The contributor is 60–69, female · the back of the torso, front of the torso, head or neck and arm are involved · the photo was captured at an angle — 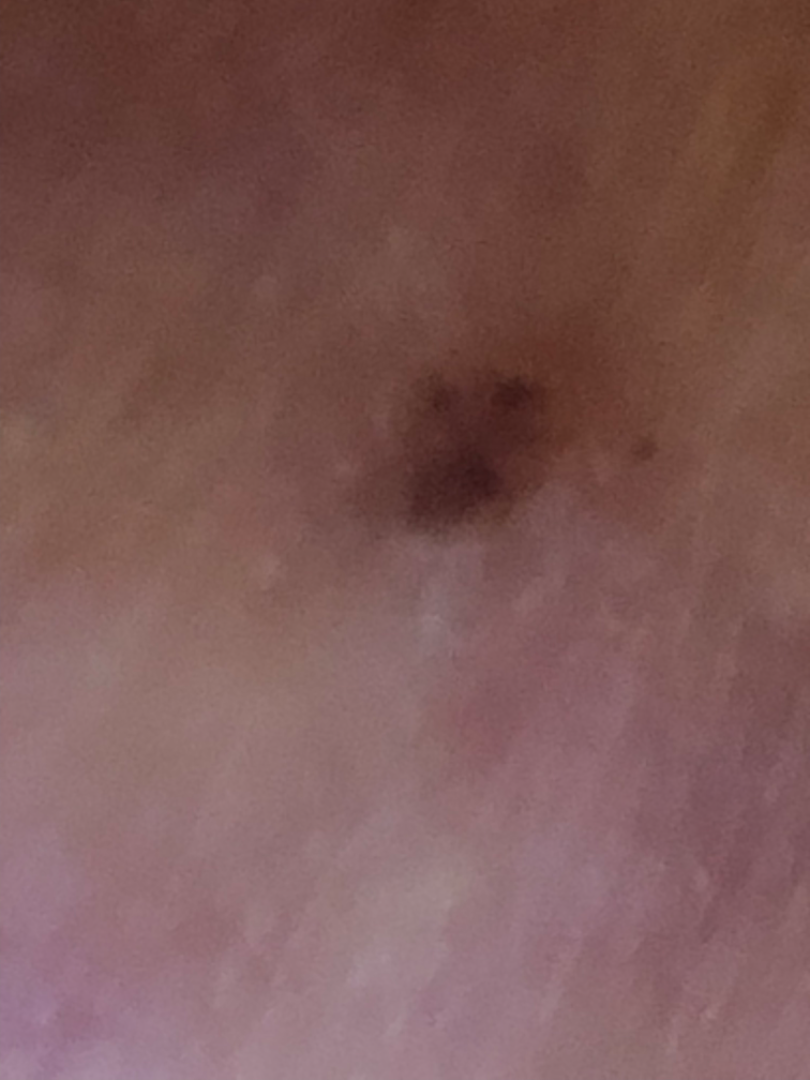The condition could not be reliably identified from the image. Self-reported Fitzpatrick III. The patient notes the lesion is rough or flaky and raised or bumpy. Symptoms reported: pain, enlargement and bothersome appearance. The patient also reports fatigue and joint pain. The condition has been present for more than five years. The patient considered this a rash.